The contributor reports the lesion is rough or flaky, a close-up photograph, the affected area is the top or side of the foot, the contributor reports the condition has been present for one to four weeks — 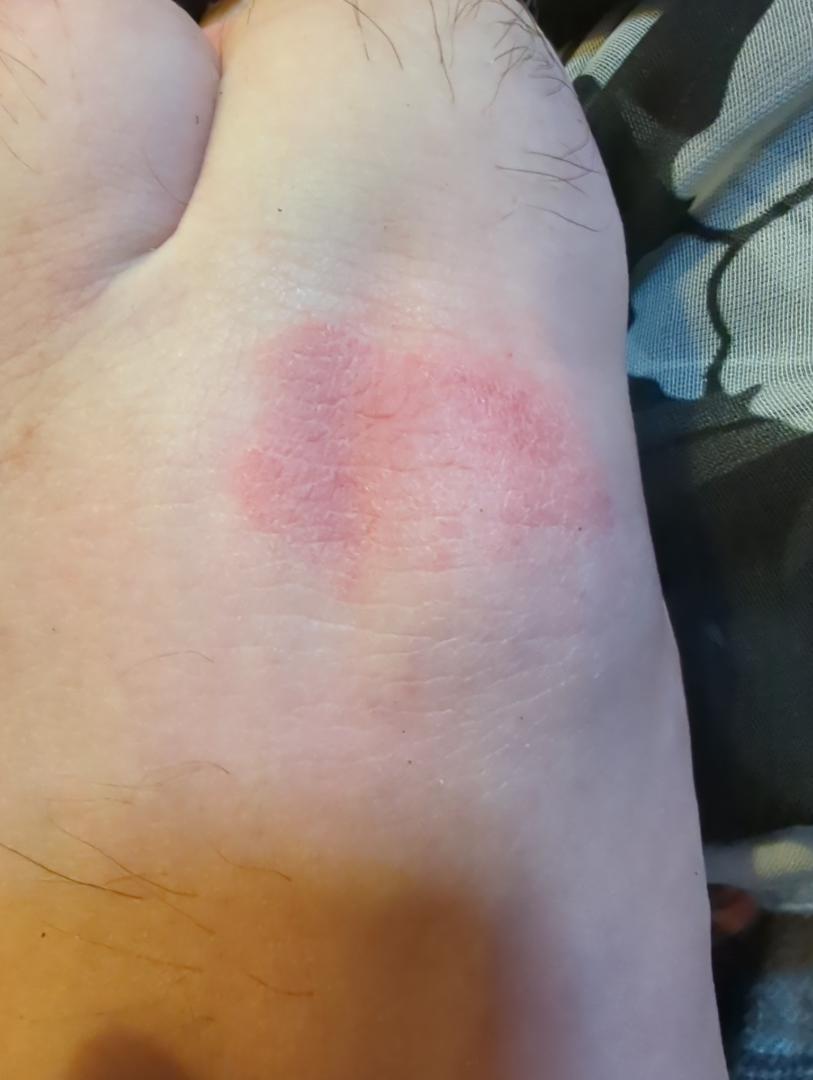{"assessment": "indeterminate from the photograph"}